A skin lesion imaged with contact-polarized dermoscopy; Fitzpatrick phototype I — 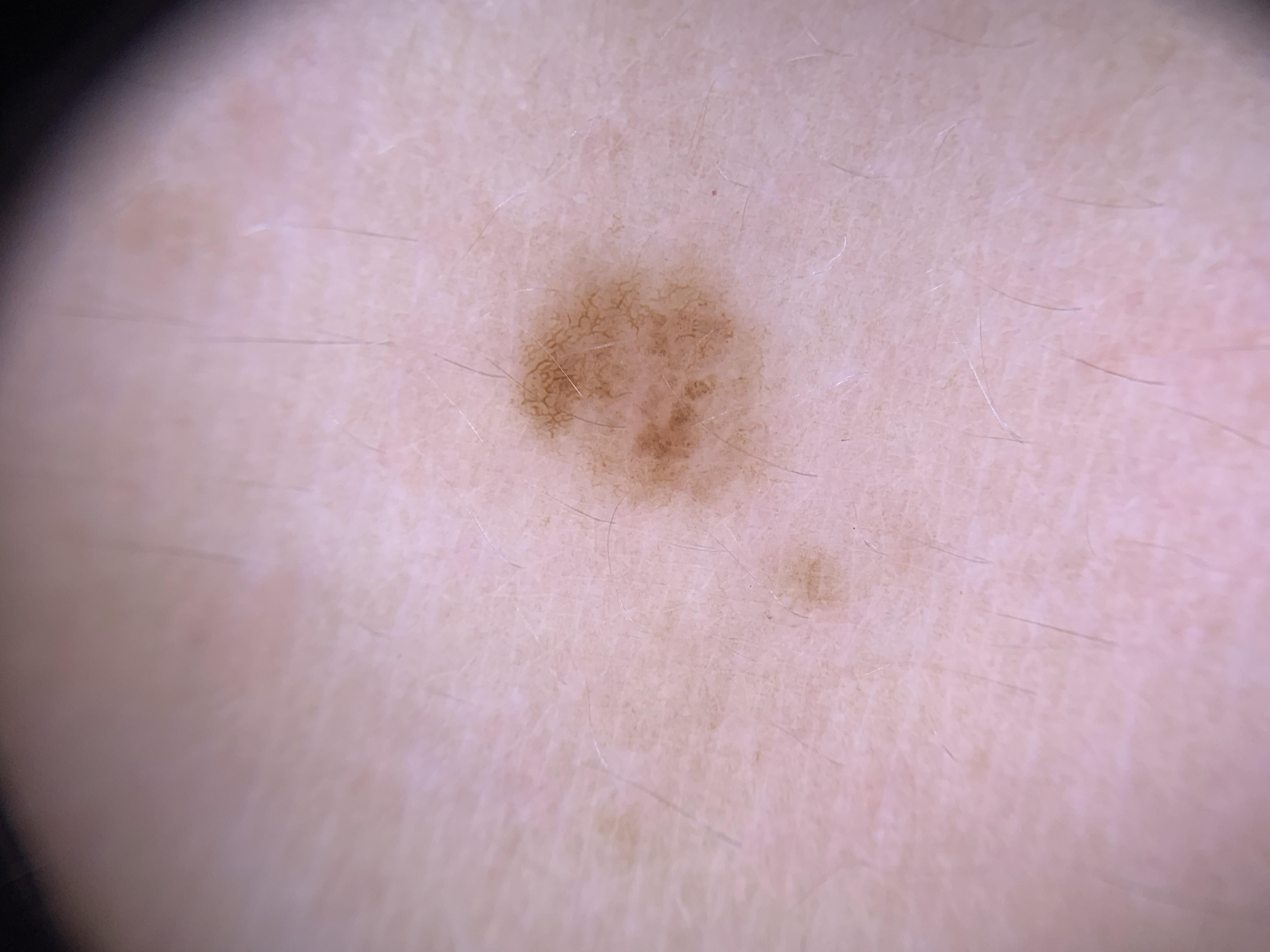Findings:
* body site: a lower extremity
* impression: Nevus